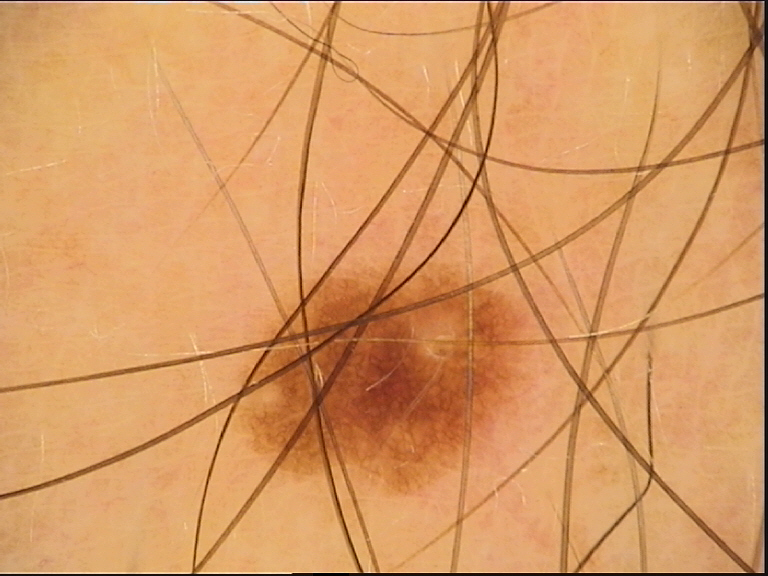Q: What is the diagnosis?
A: junctional nevus (expert consensus)